A clinical photograph of a skin lesion; recorded as Fitzpatrick skin type II; a female subject in their 60s; history notes prior skin cancer (patient or family), pesticide exposure, and prior malignancy (patient or family).
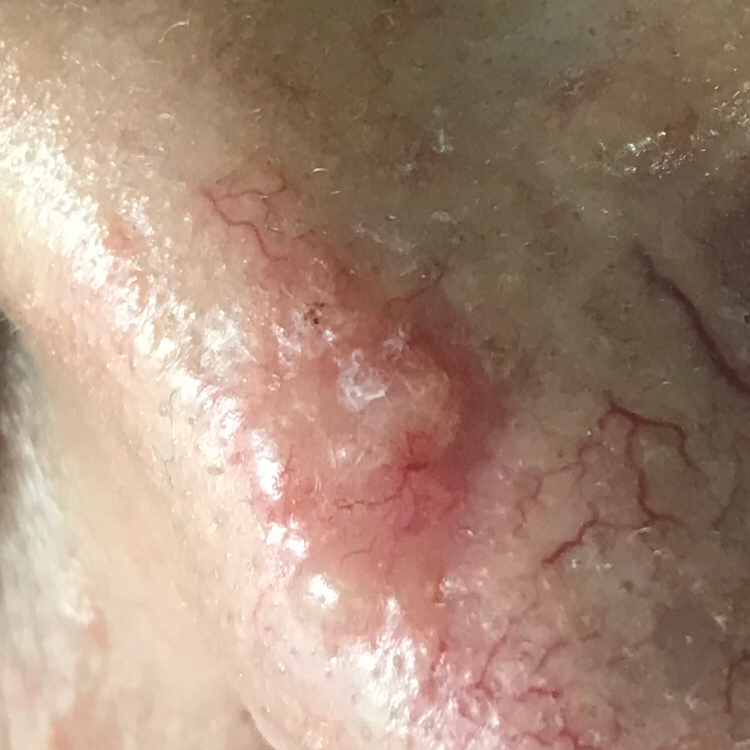Q: Any reported symptoms?
A: itching, elevation
Q: What did the workup show?
A: basal cell carcinoma (biopsy-proven)